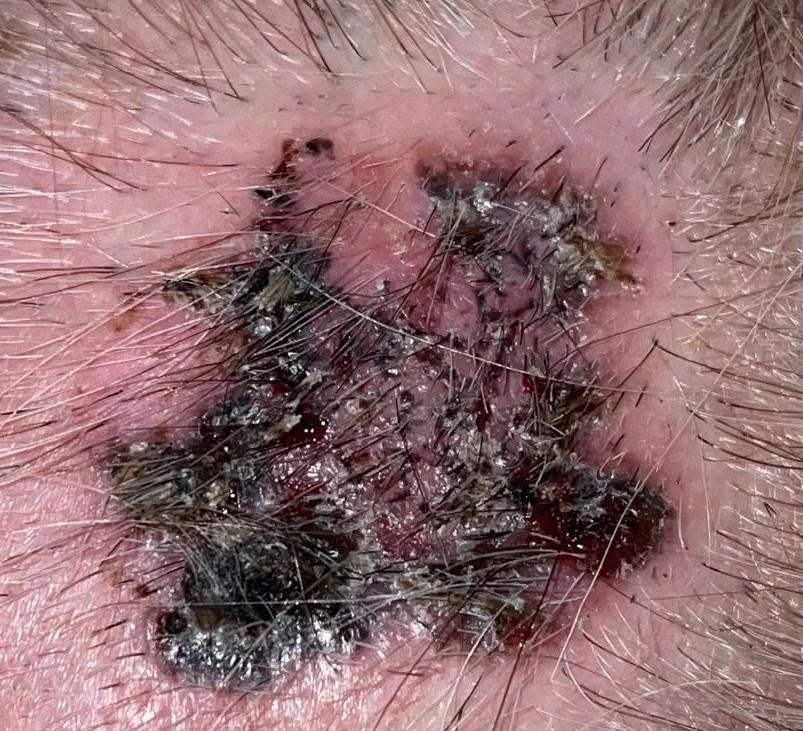Findings:
• patient · female, aged approximately 70
• skin phototype · II
• body site · the head or neck
• diagnostic label · Basal cell carcinoma (biopsy-proven)